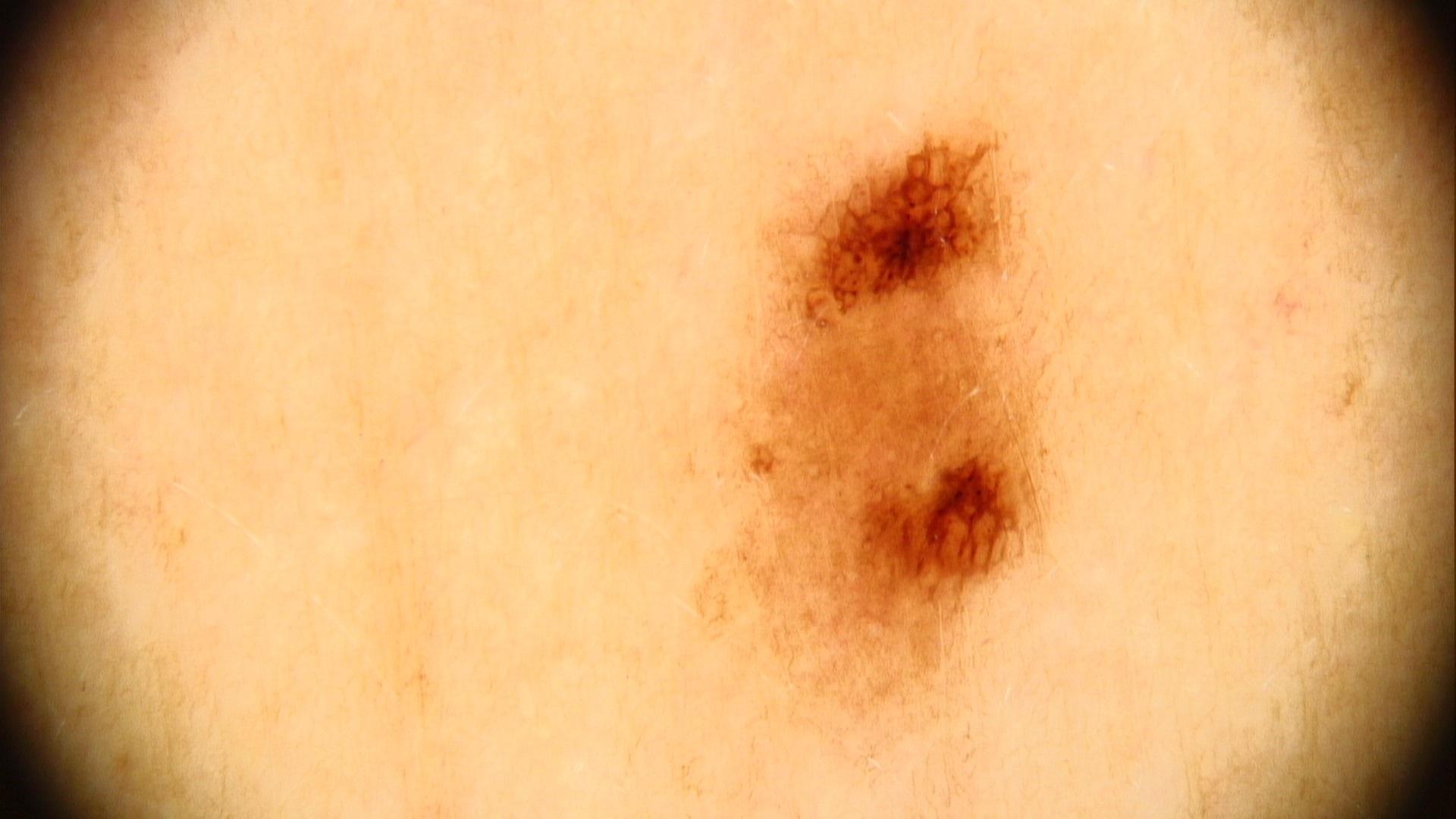{
  "patient": {
    "age_approx": 40,
    "sex": "male"
  },
  "skin_type": "III",
  "image": "dermatoscopic image",
  "lesion_location": {
    "region": "the trunk",
    "detail": "the posterior trunk"
  },
  "diagnosis": {
    "name": "Nevus",
    "malignancy": "benign",
    "confirmation": "expert clinical impression",
    "lineage": "melanocytic"
  }
}